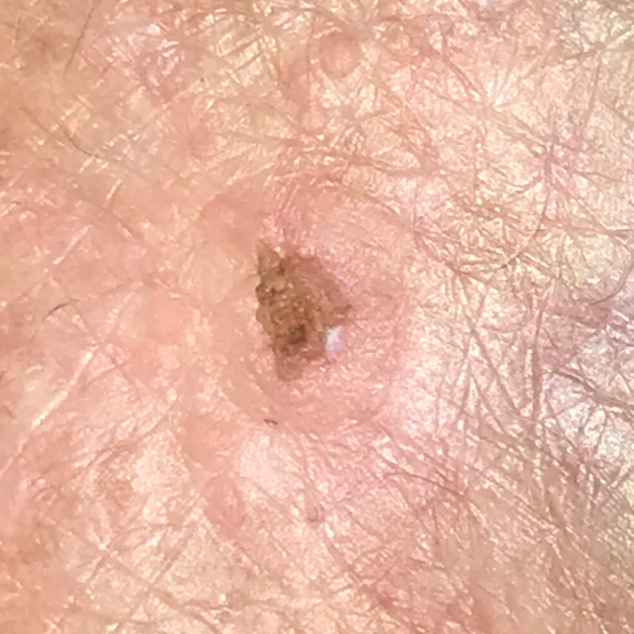History notes prior skin cancer (patient or family). The patient is Fitzpatrick phototype II. A clinical photograph of a skin lesion. A female subject aged 57. The lesion is on a hand. The lesion measures 5 × 4 mm. The patient describes that the lesion has bled, is elevated, and itches, but does not hurt. Confirmed on histopathology as a malignancy — a squamous cell carcinoma.